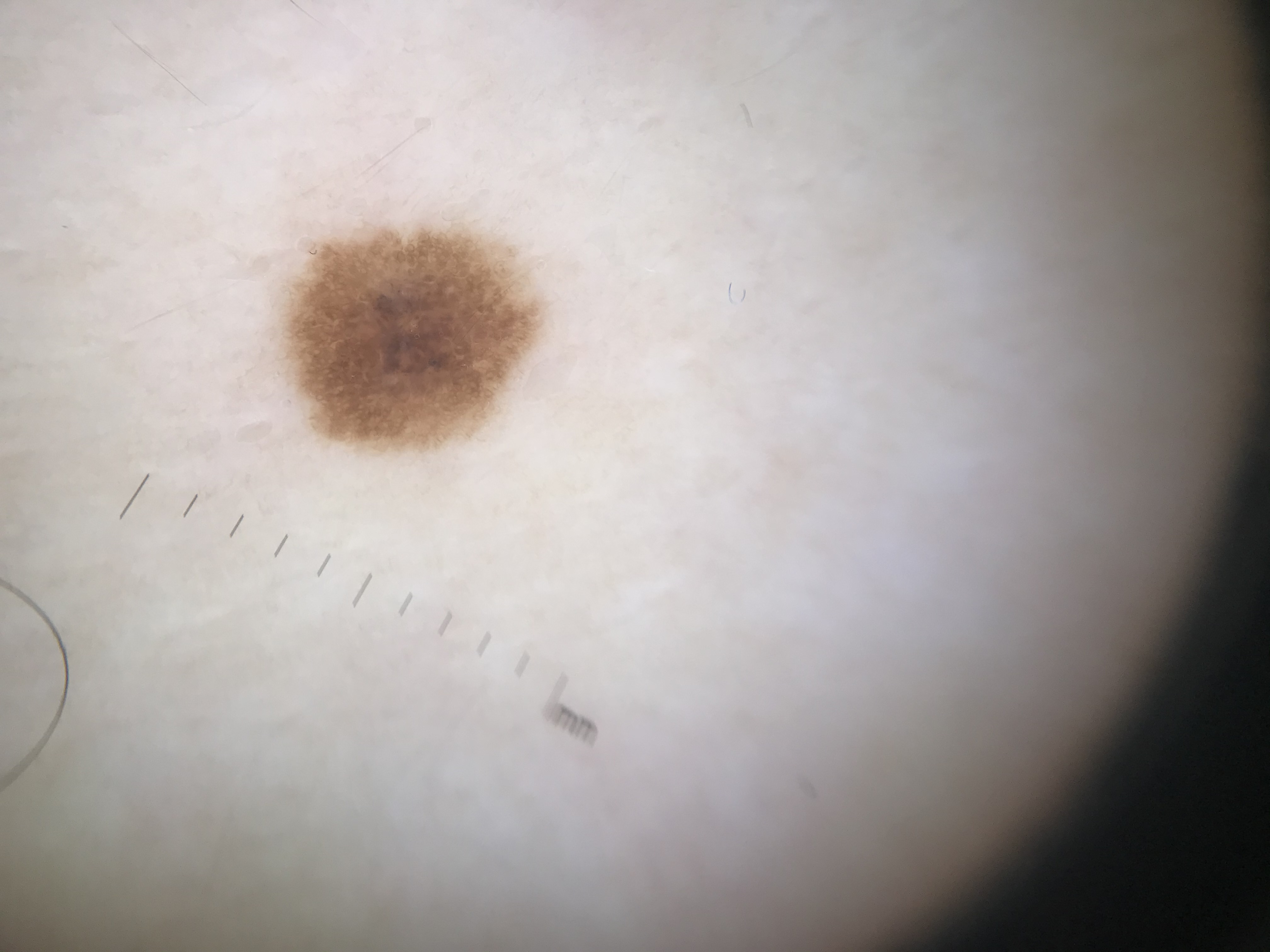diagnosis: dysplastic junctional nevus (expert consensus).